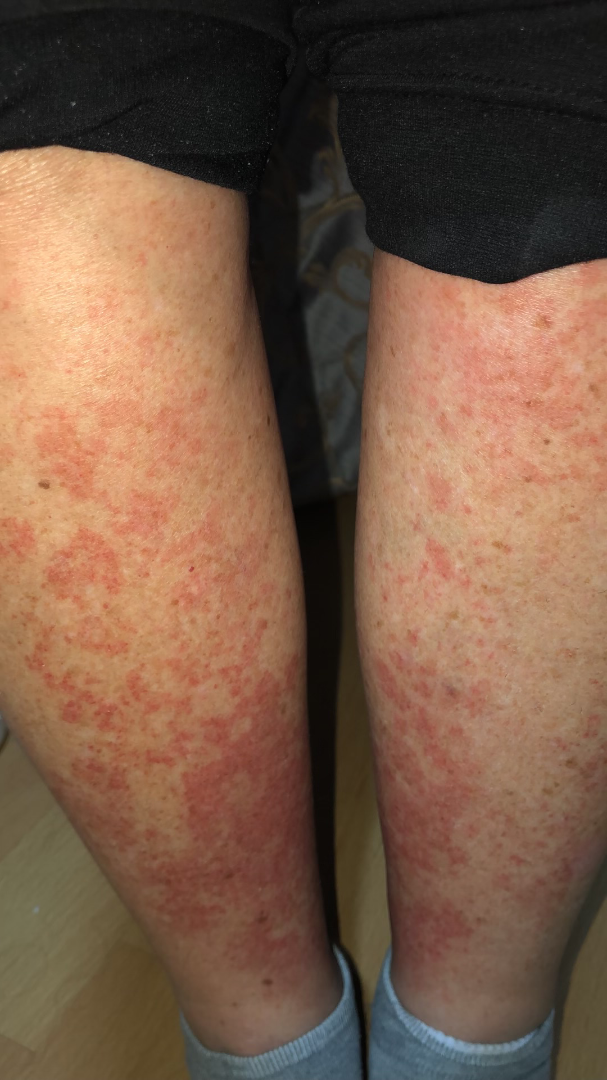assessment: unable to determine